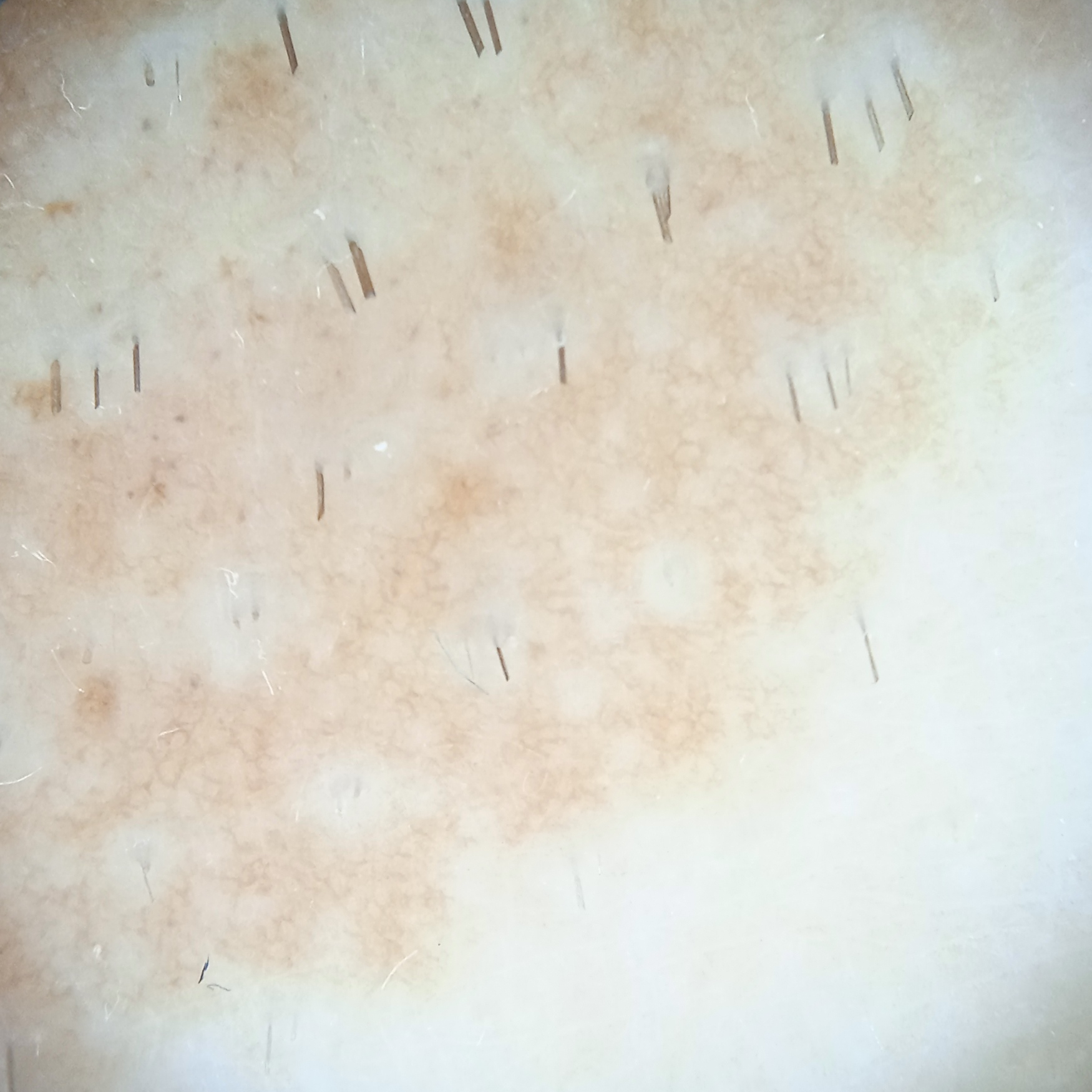Clinical context:
Dermoscopy of a skin lesion. On a questionnaire the patient reported no sunbed use and no family history of skin cancer. A male patient aged 15. The patient says their skin tans without first burning. The lesion is on an arm. The lesion measures approximately 26.1 mm.
Diagnosis:
Histopathology confirmed a melanocytic nevus, following a punch biopsy.